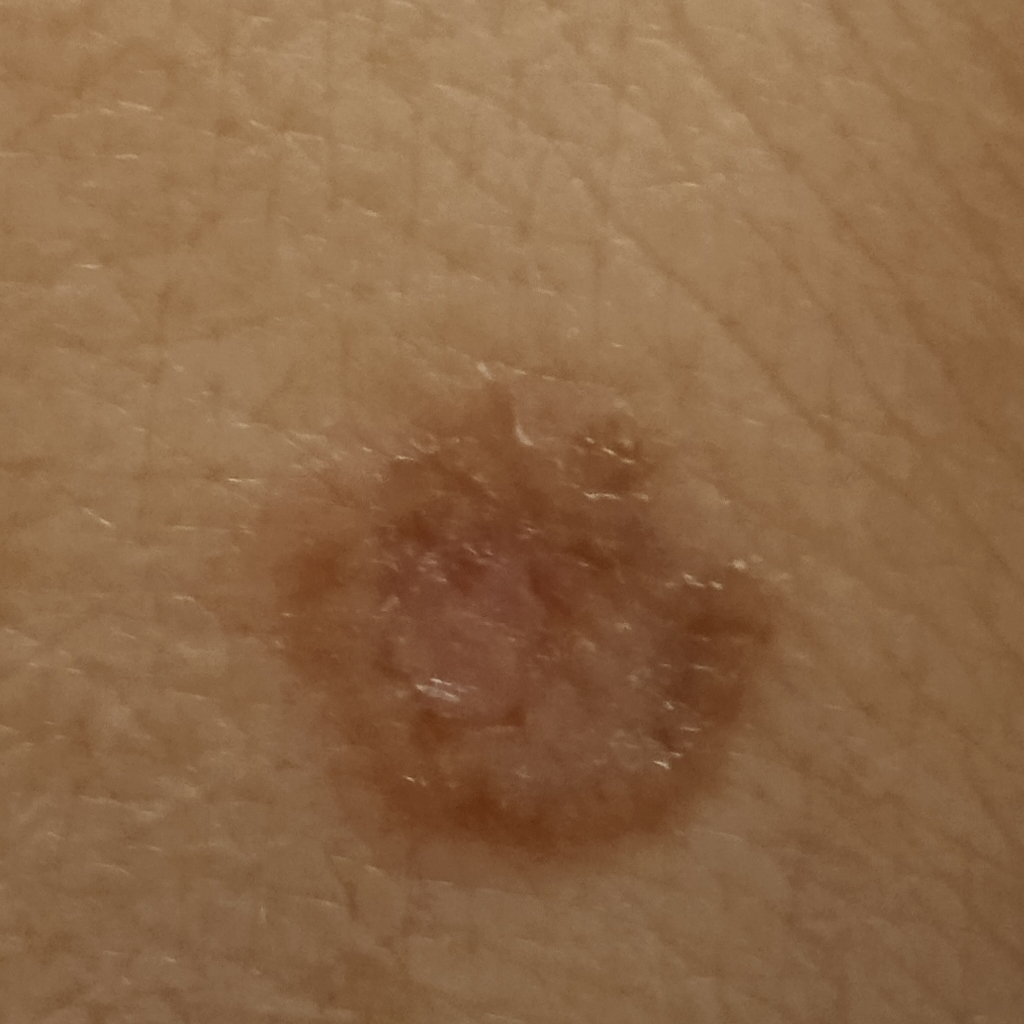Findings:
– sun reaction · skin tans without first burning
– nevus count · few melanocytic nevi overall
– subject · female, 60 years old
– relevant history · a personal history of cancer, a personal history of skin cancer
– referral · clinical suspicion of basal cell carcinoma
– body site · the torso
– diameter · 13.2 mm
– diagnosis · basal cell carcinoma (dermatologist consensus)